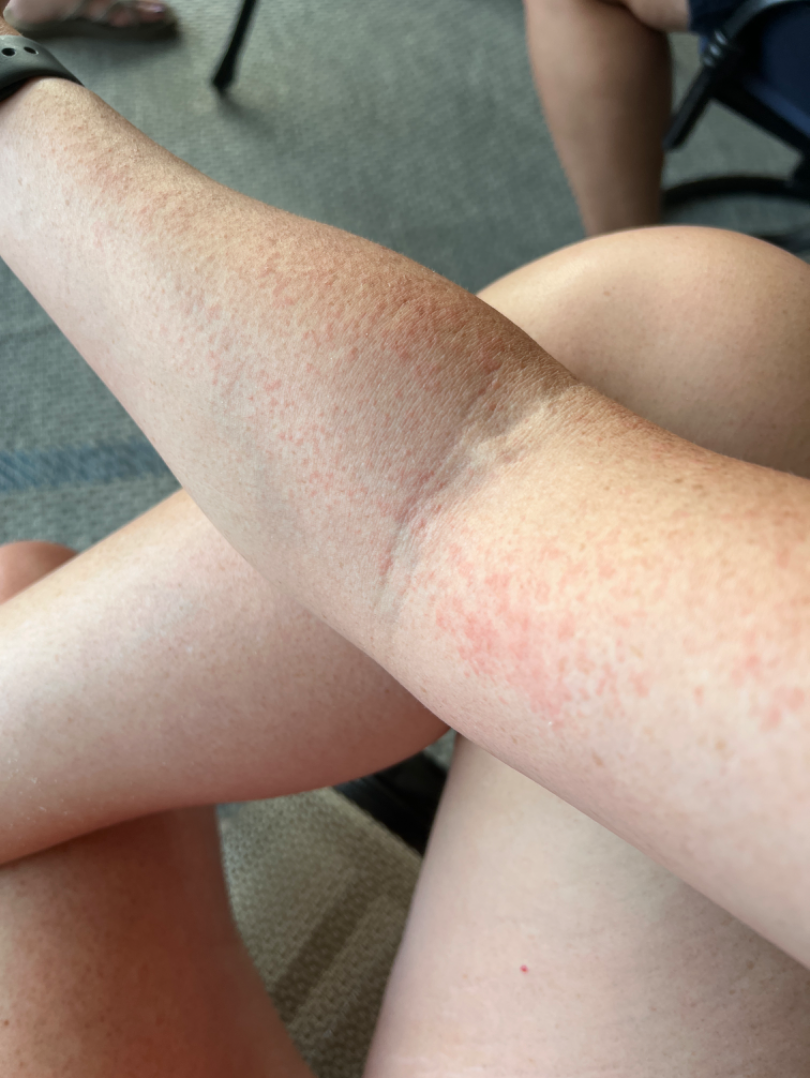Findings:
The condition could not be reliably identified from the image.
Background:
The contributor is 30–39, female. This is a close-up image. The lesion involves the leg and arm.